A dermoscopic close-up of a skin lesion — 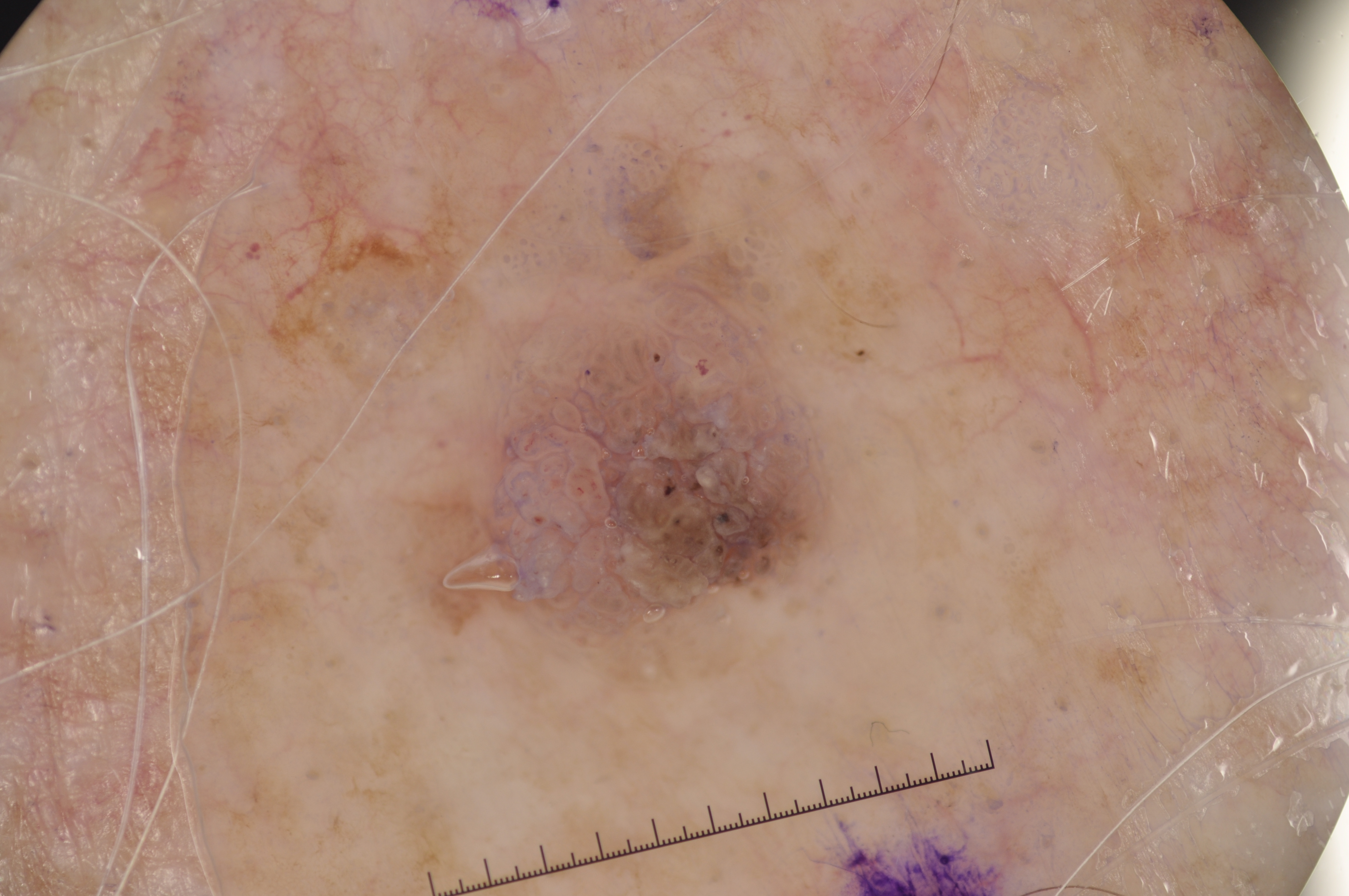<record>
  <dermoscopic_features>
    <present/>
    <absent>pigment network, streaks, milia-like cysts, negative network</absent>
  </dermoscopic_features>
  <lesion_location>
    <bbox_xyxy>395, 133, 854, 685</bbox_xyxy>
  </lesion_location>
  <lesion_extent>
    <approx_field_fraction_pct>12</approx_field_fraction_pct>
  </lesion_extent>
  <diagnosis>
    <name>seborrheic keratosis</name>
    <malignancy>benign</malignancy>
    <lineage>keratinocytic</lineage>
    <provenance>clinical</provenance>
  </diagnosis>
</record>